The patient says their skin reddens with sun exposure. A moderate number of moles by the patient's own estimate.
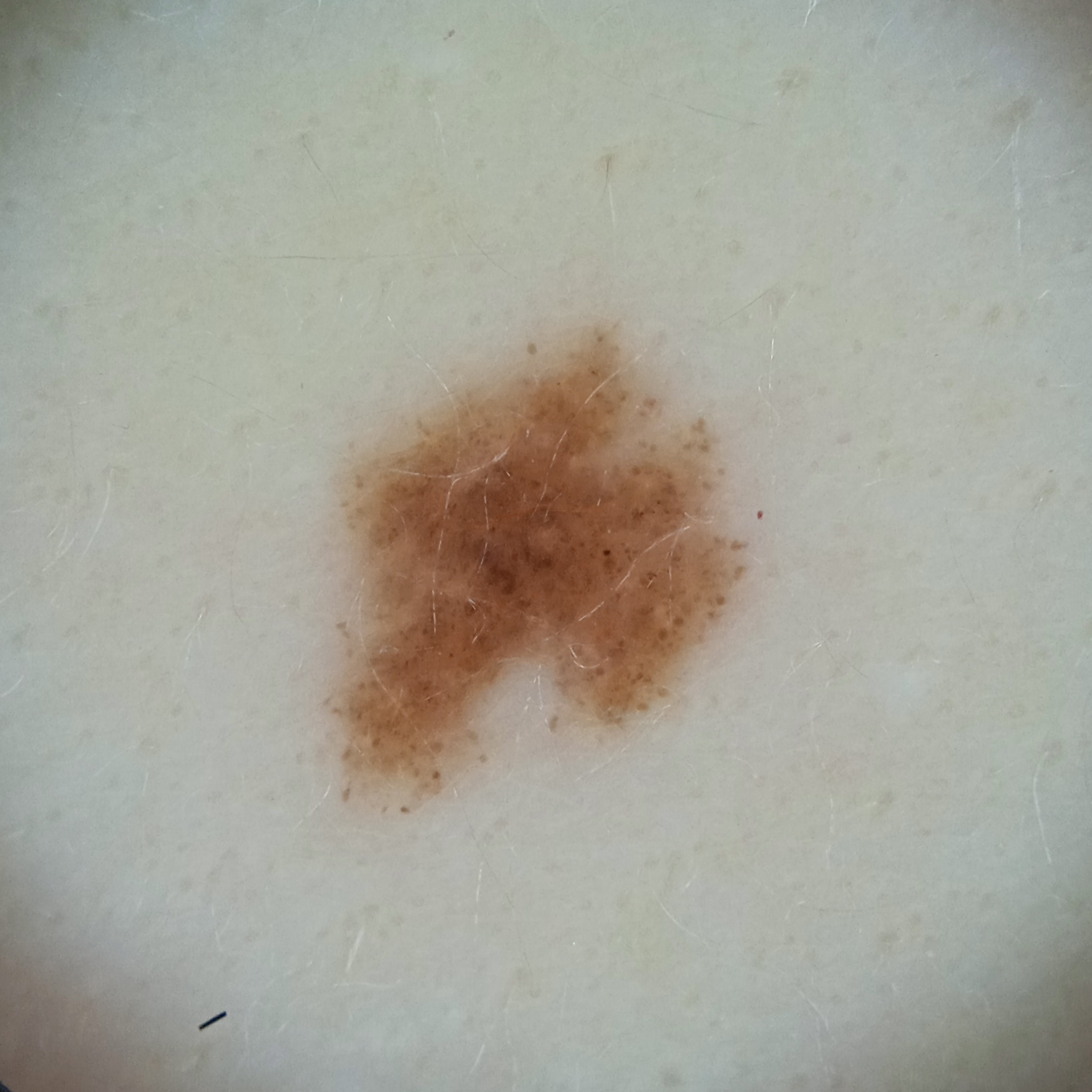{
  "lesion_location": "the back",
  "lesion_size": {
    "diameter_mm": 5.9
  },
  "diagnosis": {
    "name": "melanocytic nevus",
    "malignancy": "benign",
    "certainty": "good"
  }
}